A dermoscopic photograph of a skin lesion.
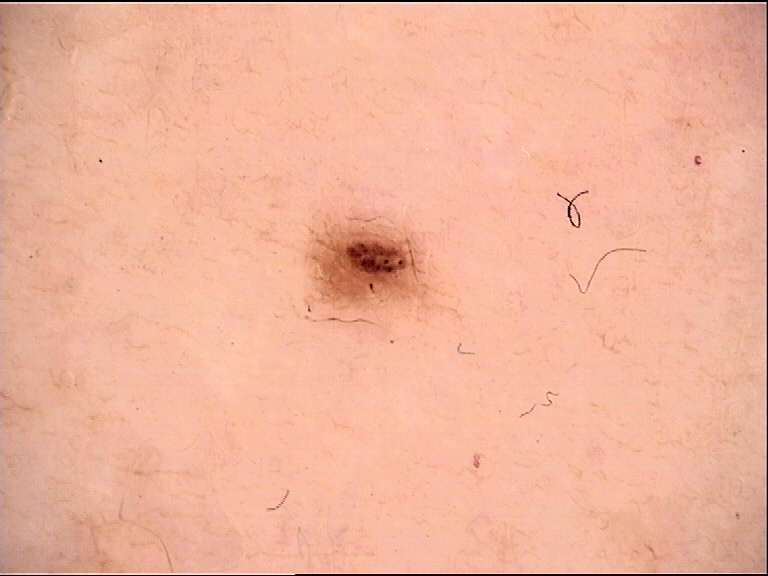diagnostic label = dysplastic junctional nevus (expert consensus)